Collected as part of a research study, without a referral diagnosis; a macroscopic clinical photograph of a skin lesion; the patient says their skin tans without first burning; a female subject 78 years of age; the patient reports no family history of skin cancer and no personal history of skin cancer.
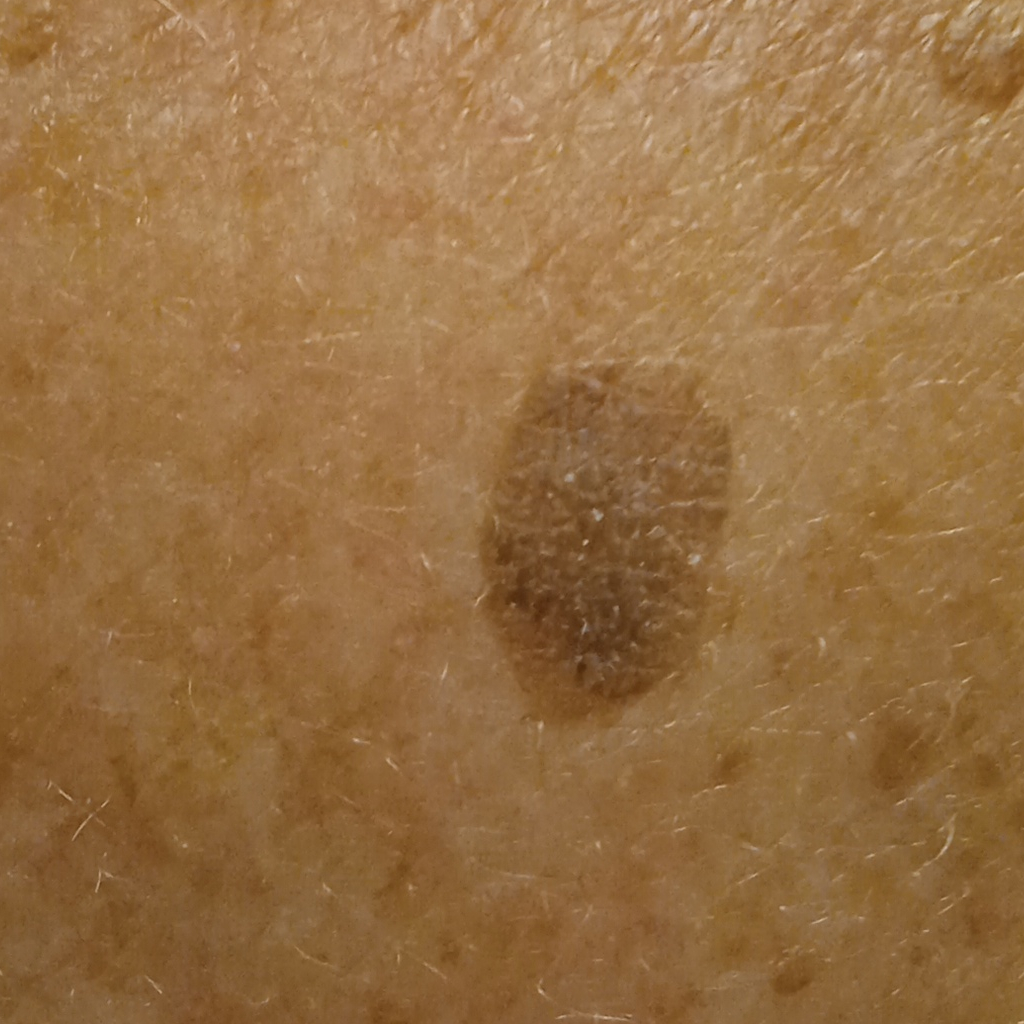site: the back
size: 9.6 mm
assessment: seborrheic keratosis (dermatologist consensus)